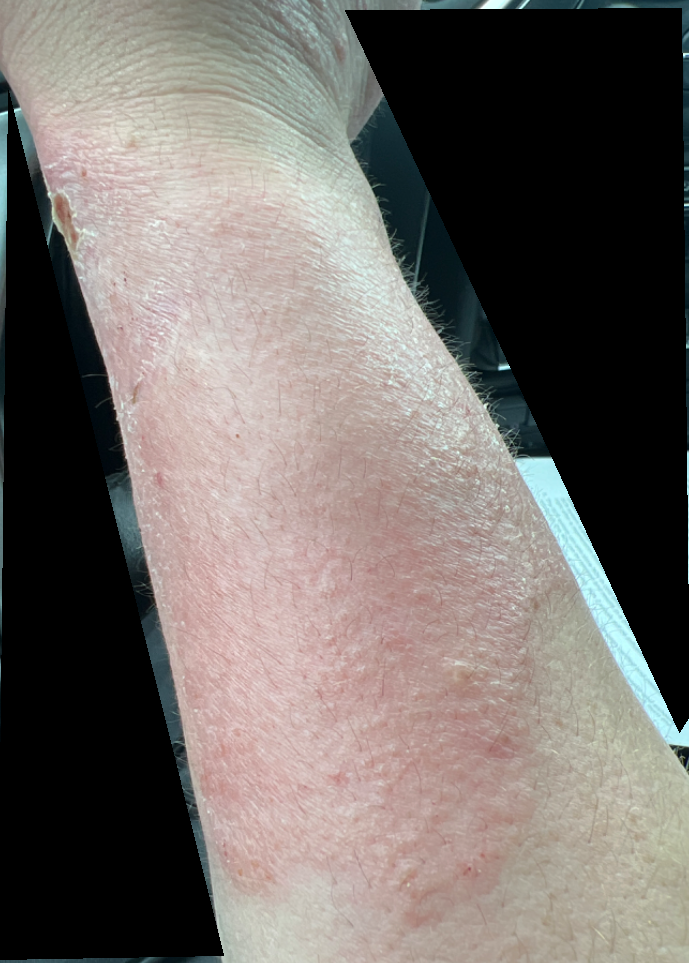Q: What is the framing?
A: close-up
Q: Where on the body?
A: arm
Q: Patient demographics?
A: male, age 18–29
Q: What is the dermatologist's impression?
A: the differential, in no particular order, includes Tinea and Allergic Contact Dermatitis